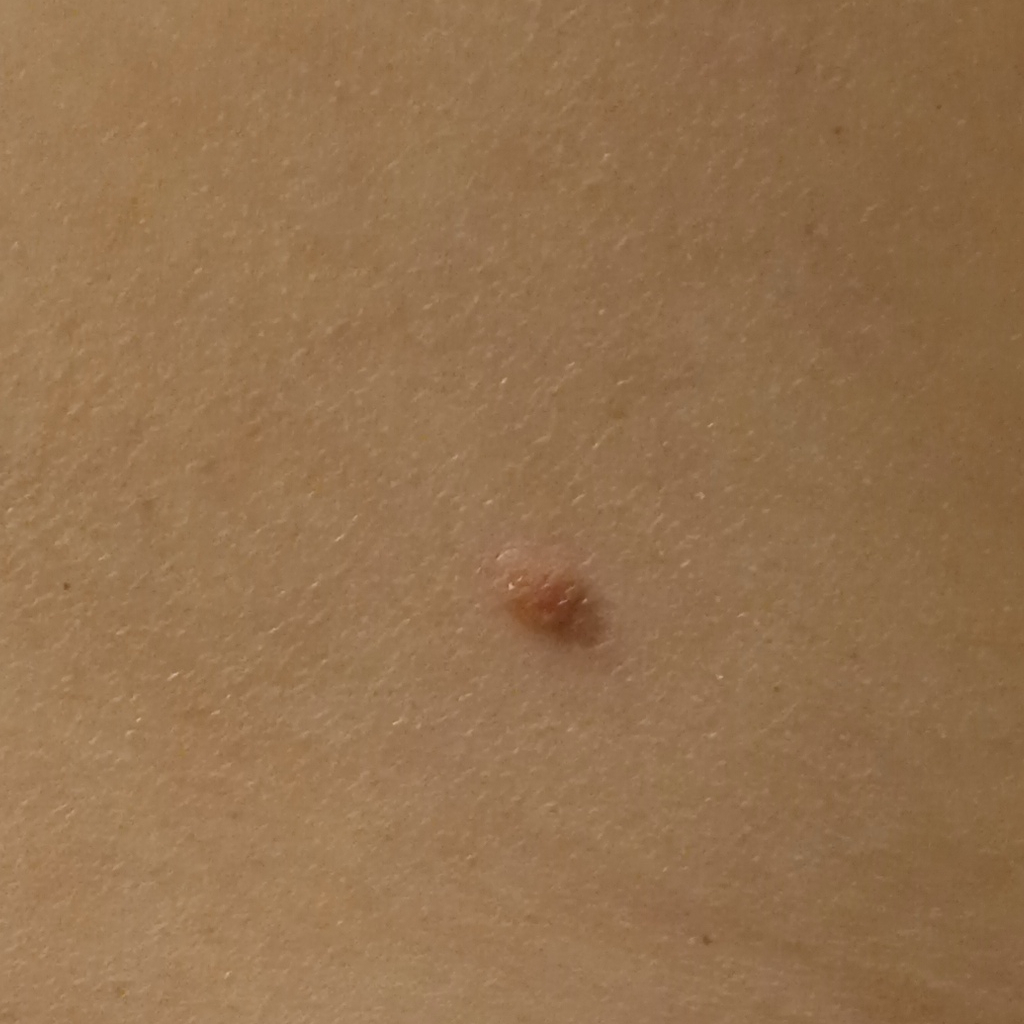imaging = clinical photograph | nevus count = few melanocytic nevi overall | pathology = basal cell carcinoma (biopsy-proven).